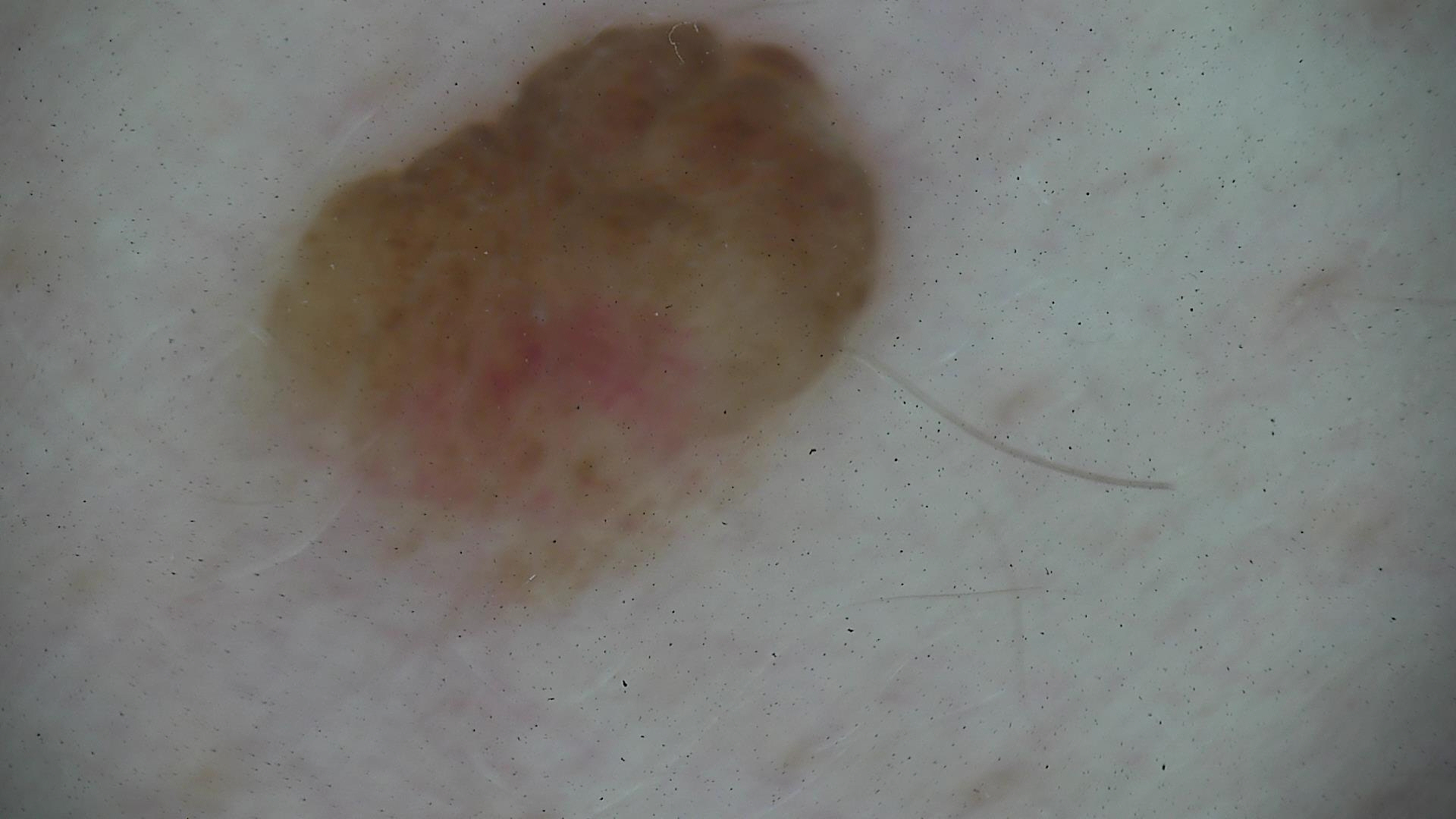Dermoscopy of a skin lesion. This is a banal lesion. Classified as a dermal nevus.